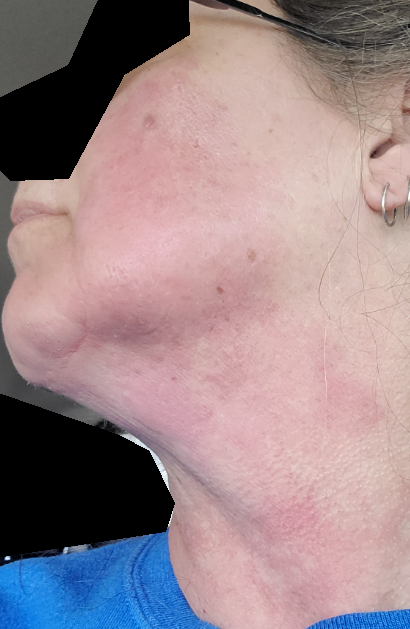Background: The patient considered this a rash. Reported duration is one to four weeks. Reported lesion symptoms include burning, bothersome appearance, enlargement and itching. The patient is 60–69, female. No associated systemic symptoms reported. Texture is reported as flat. Fitzpatrick II; human graders estimated a Monk skin tone scale of 2. The photo was captured at a distance. The head or neck is involved.